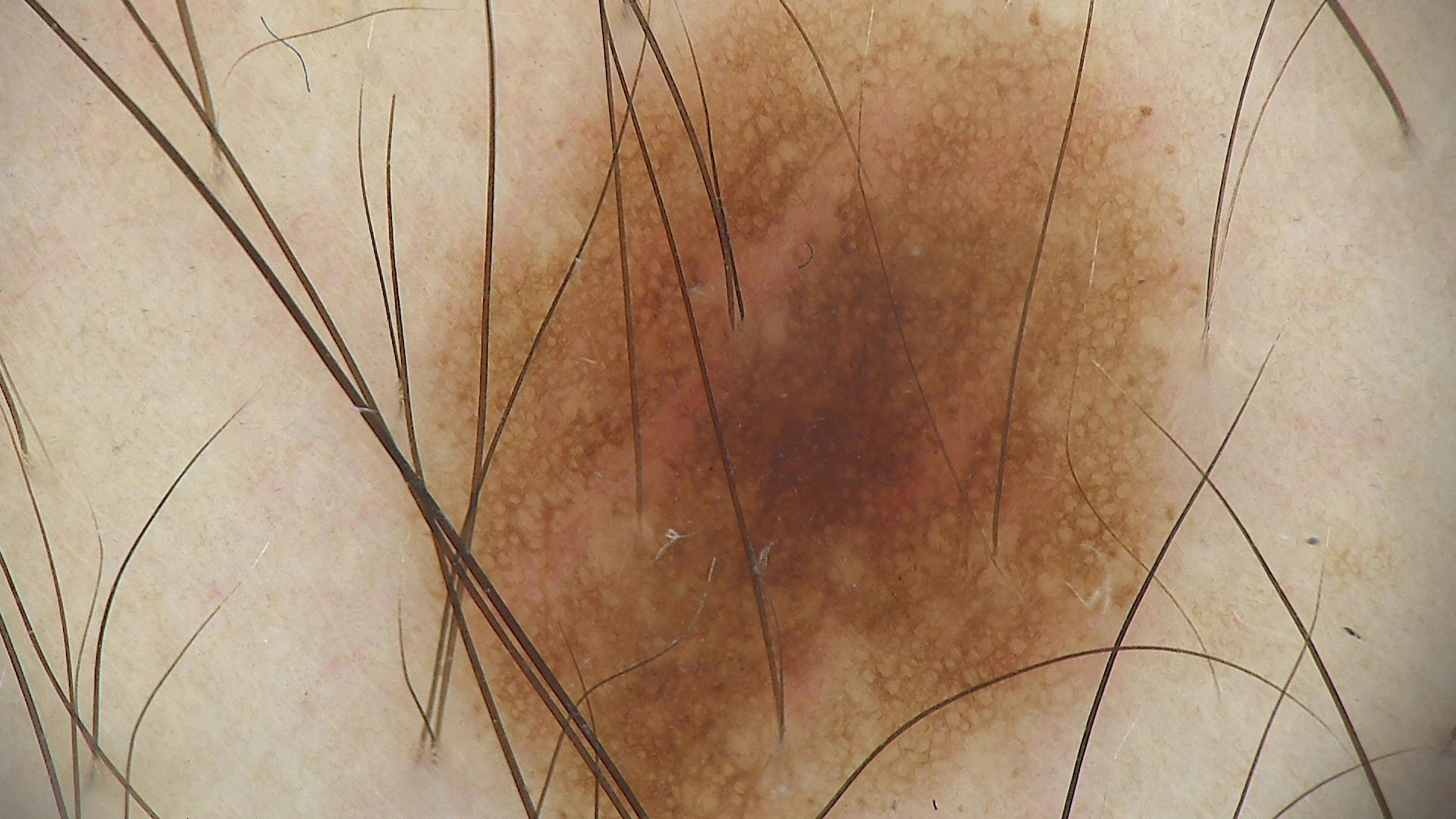image = dermatoscopy; diagnostic label = dysplastic junctional nevus (expert consensus).